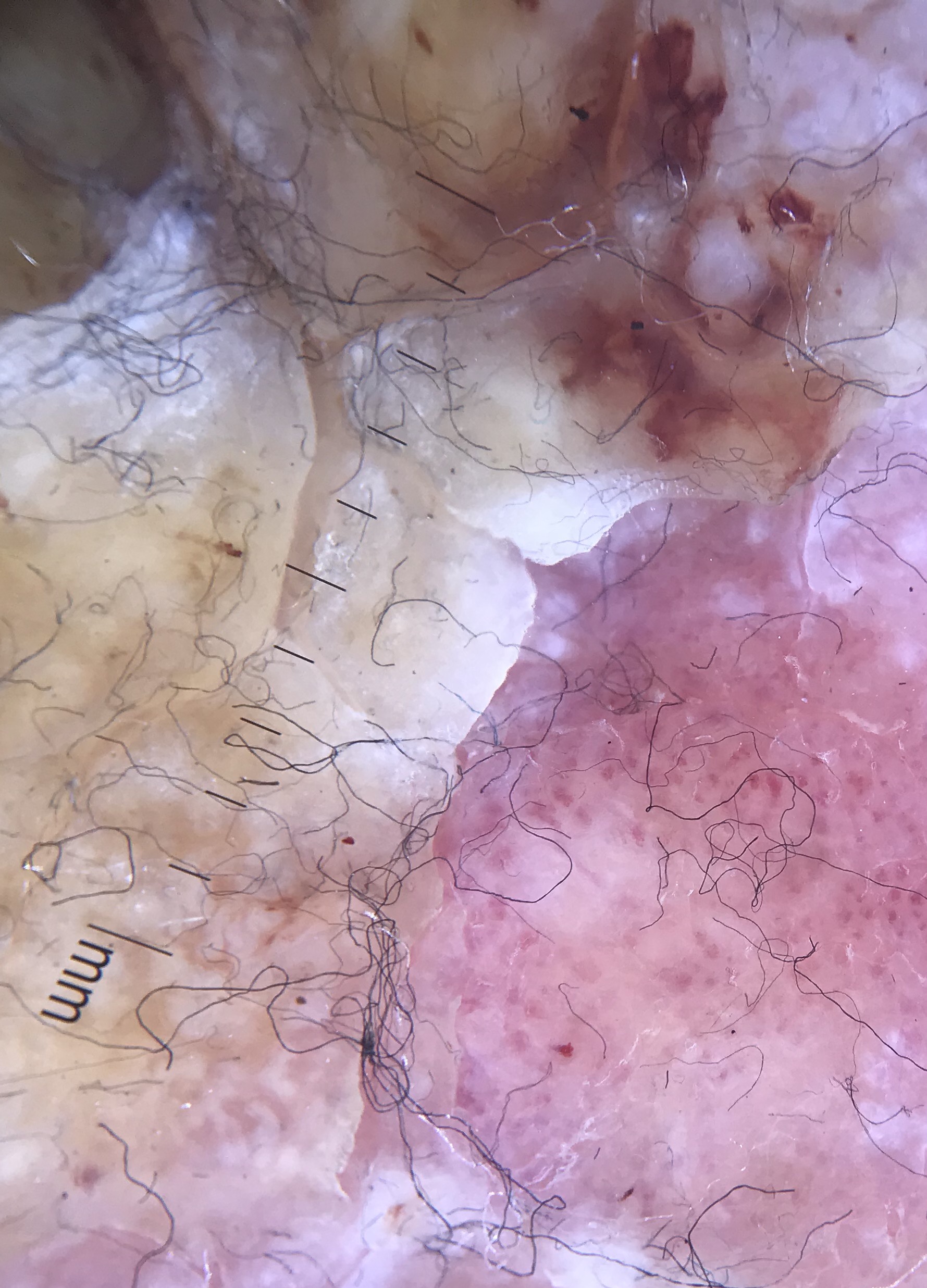imaging=dermatoscopy
lesion type=keratinocytic
pathology=squamous cell carcinoma (biopsy-proven)